A female patient aged 78-82 · dermoscopy of a skin lesion:
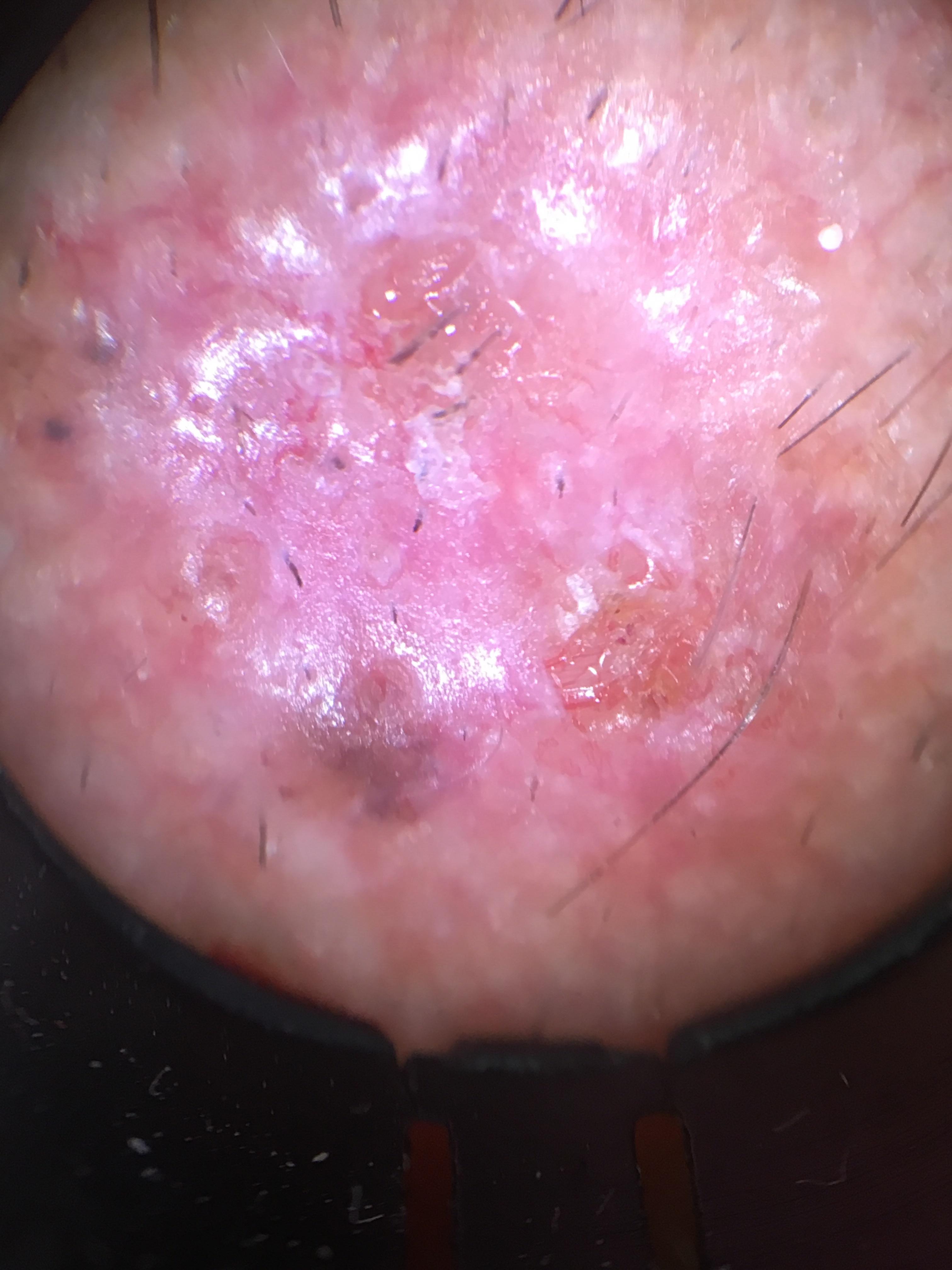<record>
<lesion_location>
<region>the head or neck</region>
</lesion_location>
<diagnosis>
<name>Basal cell carcinoma</name>
<malignancy>malignant</malignancy>
<confirmation>histopathology</confirmation>
<lineage>adnexal</lineage>
</diagnosis>
</record>